A dermoscopic photograph of a skin lesion.
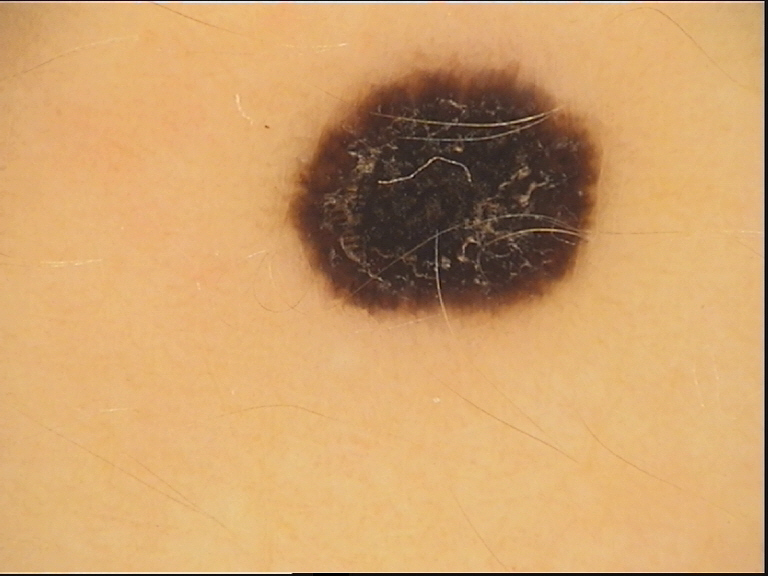| key | value |
|---|---|
| subtype | keratinocytic |
| class | seborrheic keratosis (expert consensus) |